The lesion involves the arm and head or neck · the contributor is 18–29, female · close-up view — 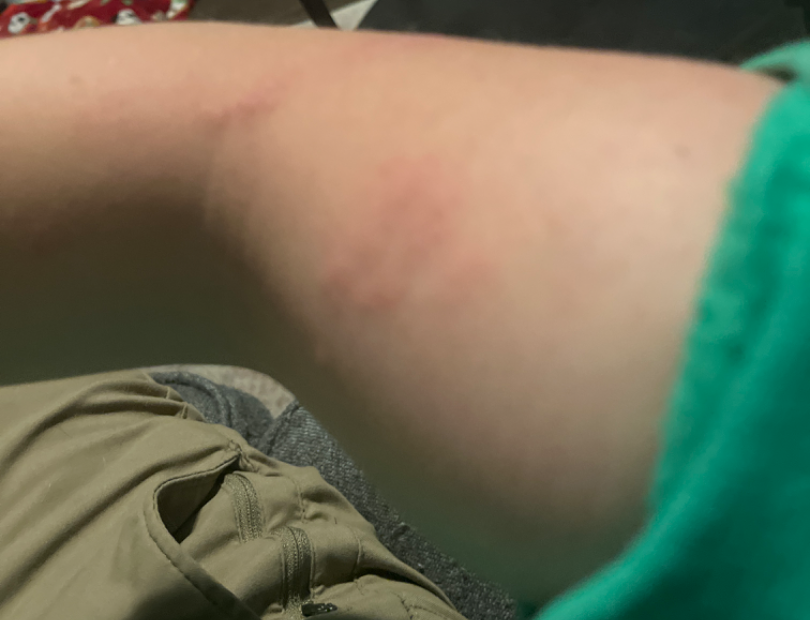Impression: Diagnostic features were not clearly distinguishable in this photograph. History: Texture is reported as raised or bumpy and rough or flaky. Reported lesion symptoms include itching. Reported duration is less than one week. No associated systemic symptoms reported.